The patient notes the condition has been present for one to three months. The patient considered this a rash. The patient notes the lesion is raised or bumpy and rough or flaky. No constitutional symptoms were reported. The patient notes itching, pain and burning. The top or side of the foot is involved. The photograph was taken at an angle: 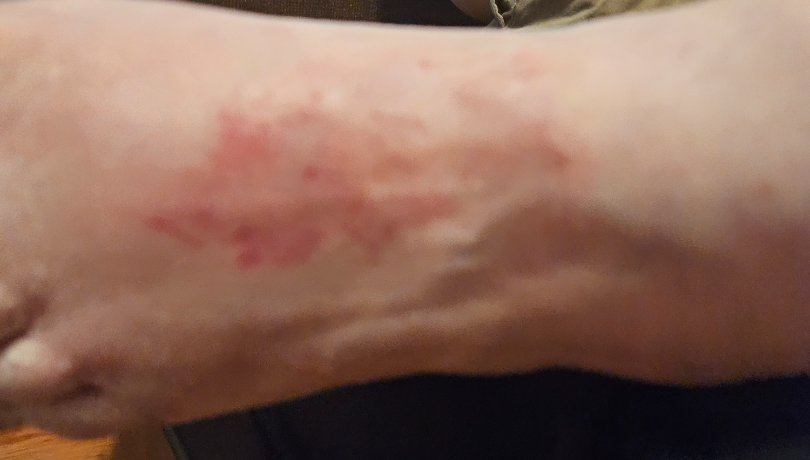Findings:
- diagnostic considerations — a single dermatologist reviewed the case: the leading impression is Tinea; also on the differential is Eczema; an alternative is Allergic Contact Dermatitis